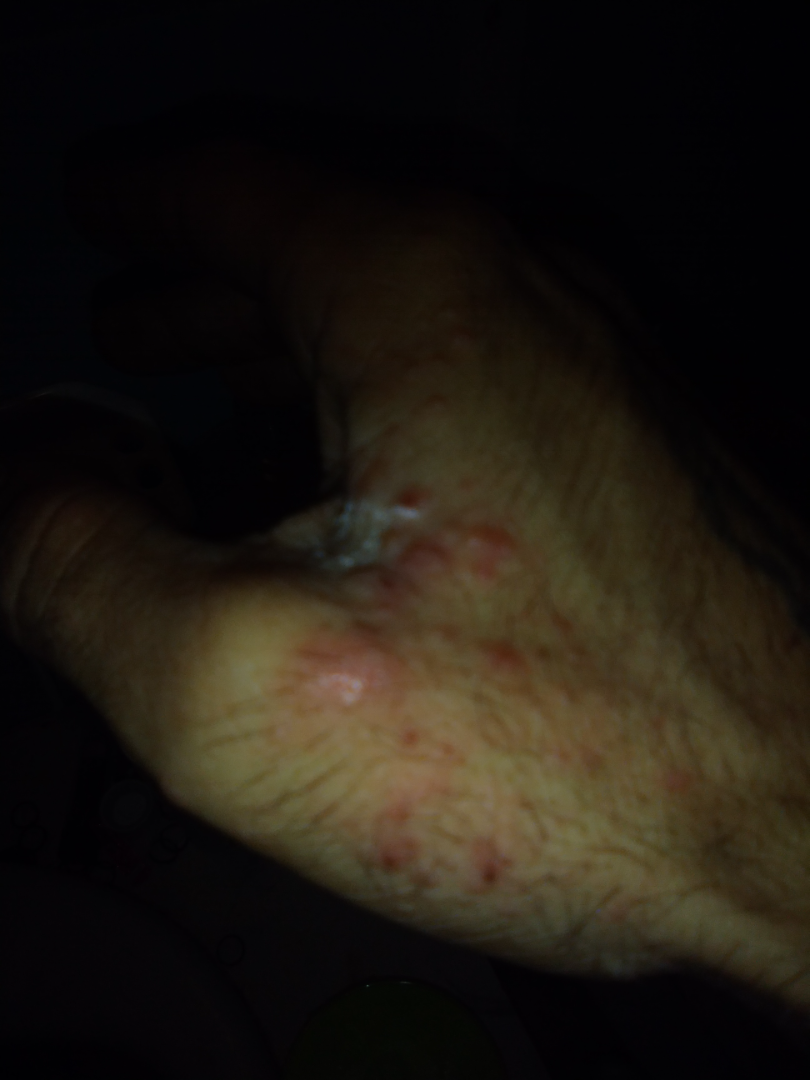Findings:
The condition could not be reliably identified from the image.
Background:
The photo was captured at a distance. The affected area is the arm, front of the torso and head or neck.